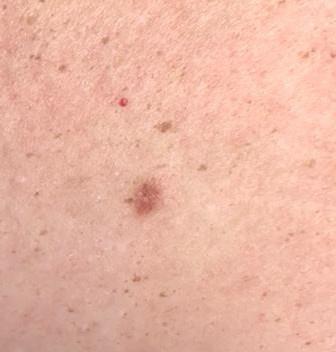A clinical photograph of a skin lesion. Fitzpatrick phototype III. A female patient in their mid-50s. Located on a lower extremity. Clinically diagnosed as a benign, fibro-histiocytic lesion — a dermatofibroma.